The patient is 18–29, female · the lesion involves the arm · an image taken at a distance.
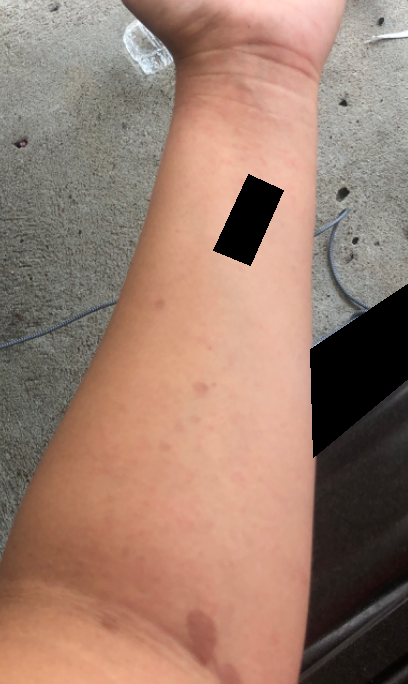Patient information: The patient considered this a rash. The patient indicates the condition has been present for less than one week. The patient indicates itching and bothersome appearance. Review: Acute dermatitis, NOS and Eczema were each considered, in no particular order.